This is a dermoscopic photograph of a skin lesion:
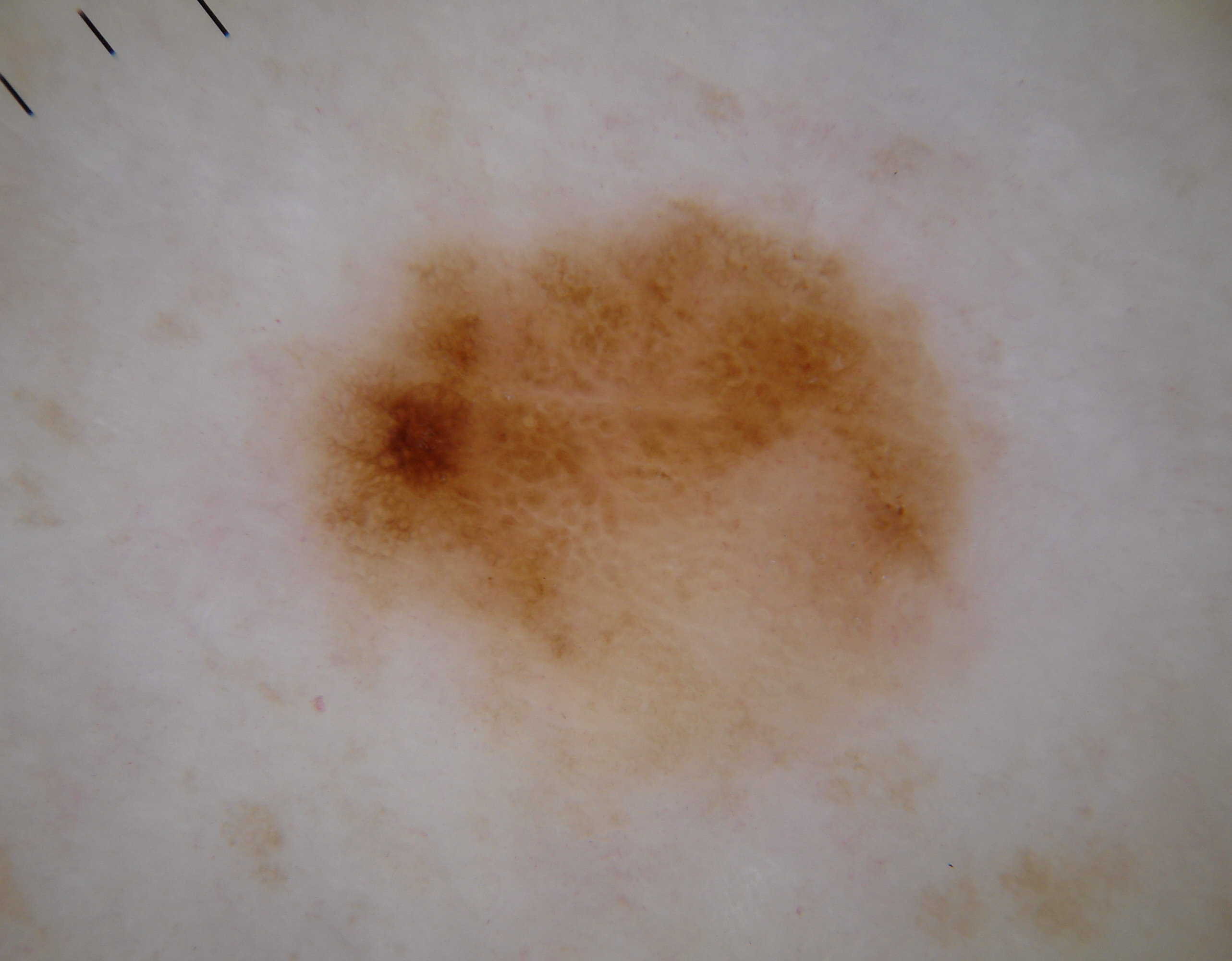Notes:
- extent · ~33% of the field
- lesion bbox · (285, 186, 1011, 840)
- features · negative network and pigment network; absent: milia-like cysts, globules, and streaks
- impression · a melanocytic nevus